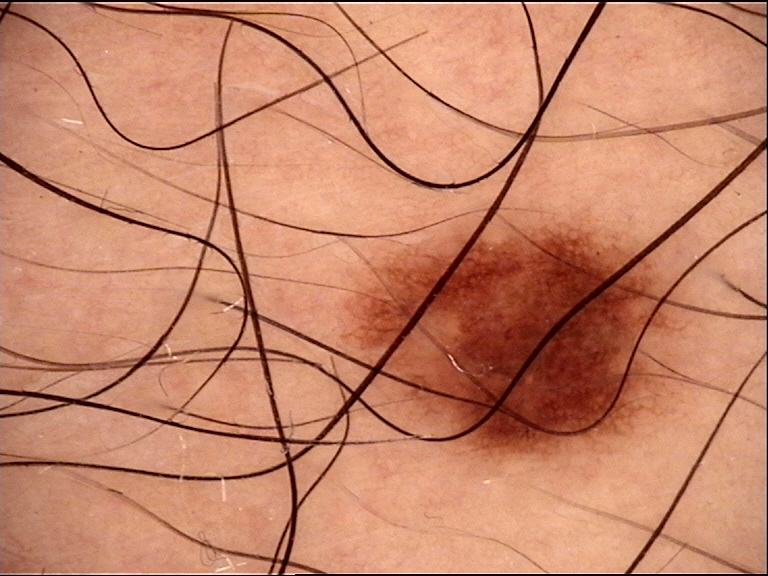The diagnosis was a benign lesion — a dysplastic junctional nevus.